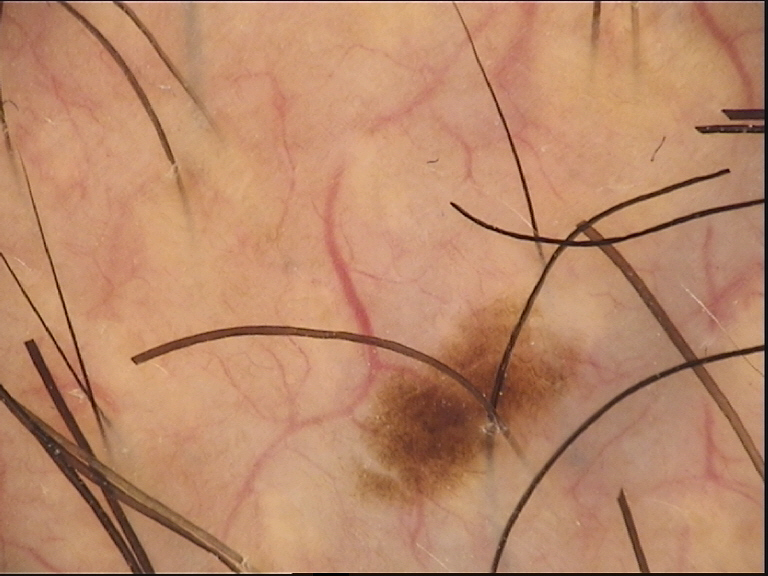Consistent with a dysplastic junctional nevus.